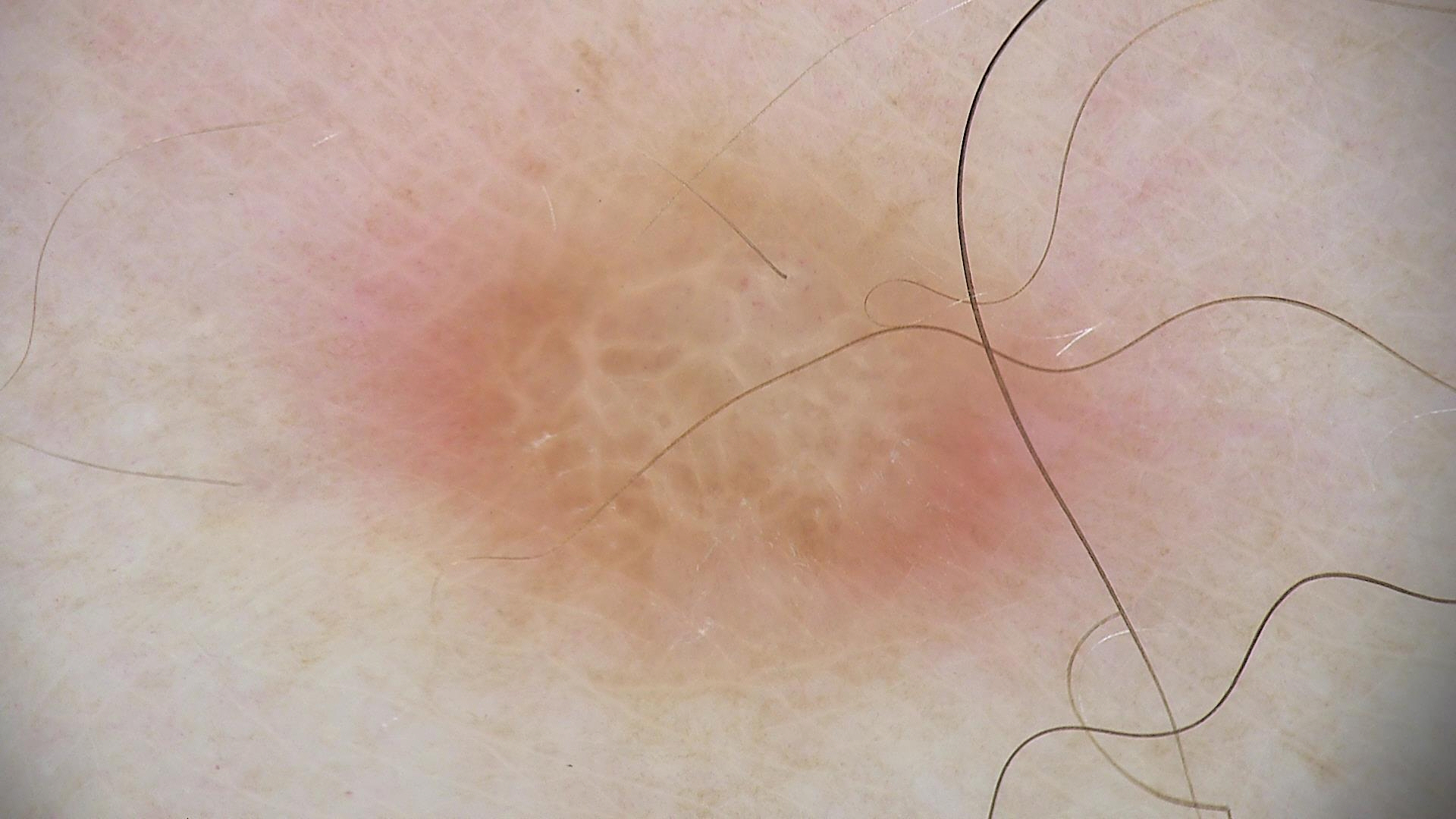<case>
  <diagnosis>
    <name>dermatofibroma</name>
    <code>df</code>
    <malignancy>benign</malignancy>
    <super_class>non-melanocytic</super_class>
    <confirmation>expert consensus</confirmation>
  </diagnosis>
</case>